Symptoms reported: burning, enlargement, darkening, bothersome appearance and pain. Reported duration is one to four weeks. The photograph was taken at an angle. The patient reported no systemic symptoms. The lesion involves the top or side of the foot. Female subject, age 40–49.
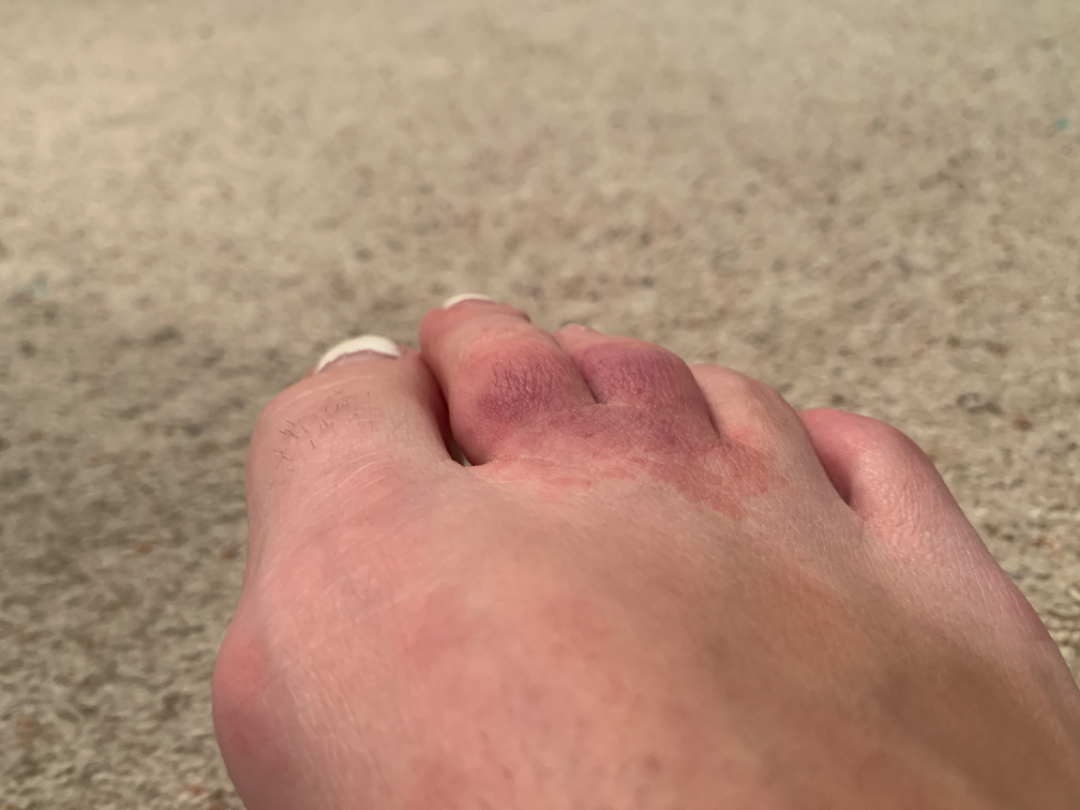Findings:
On remote dermatologist review, Acute and chronic dermatitis and Allergic Contact Dermatitis were each considered, in no particular order.